Reported duration is less than one week; the affected area is the leg; the patient considered this a rash; an image taken at an angle; no relevant systemic symptoms; texture is reported as raised or bumpy; the subject is a female aged 18–29.
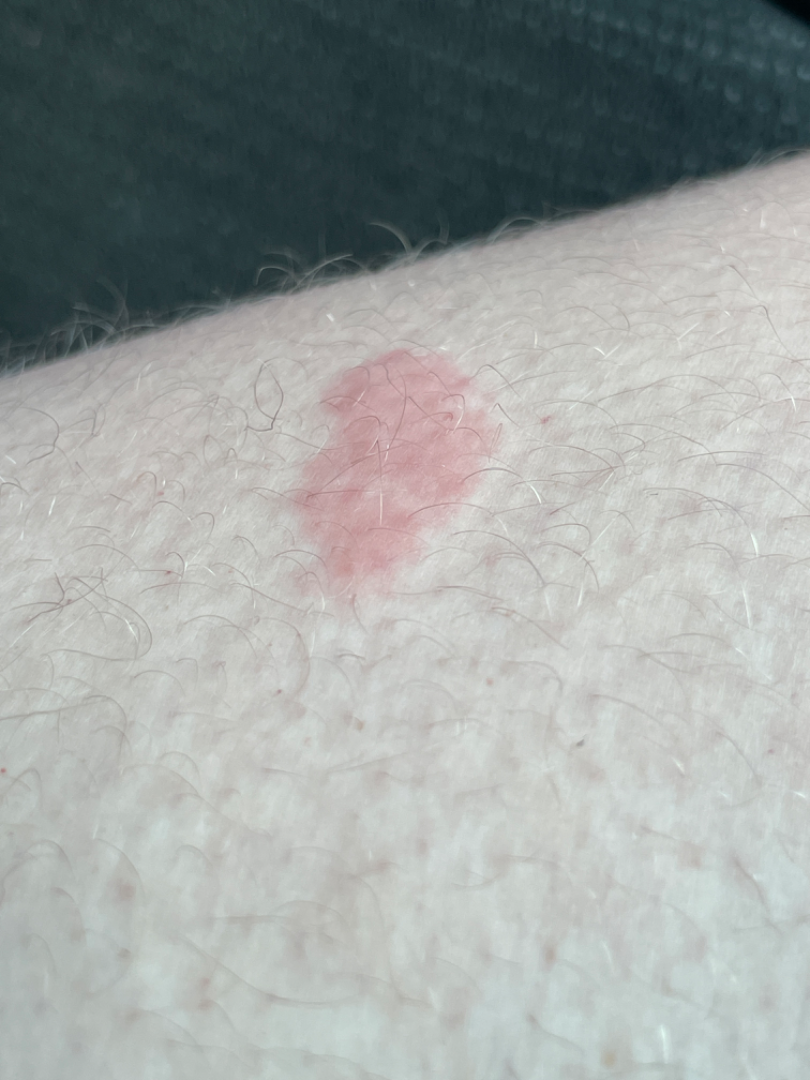The image was not sufficient for the reviewer to characterize the skin condition.